A female subject age 64 · referred with a clinical suspicion of basal cell carcinoma · a dermoscopic image of a skin lesion.
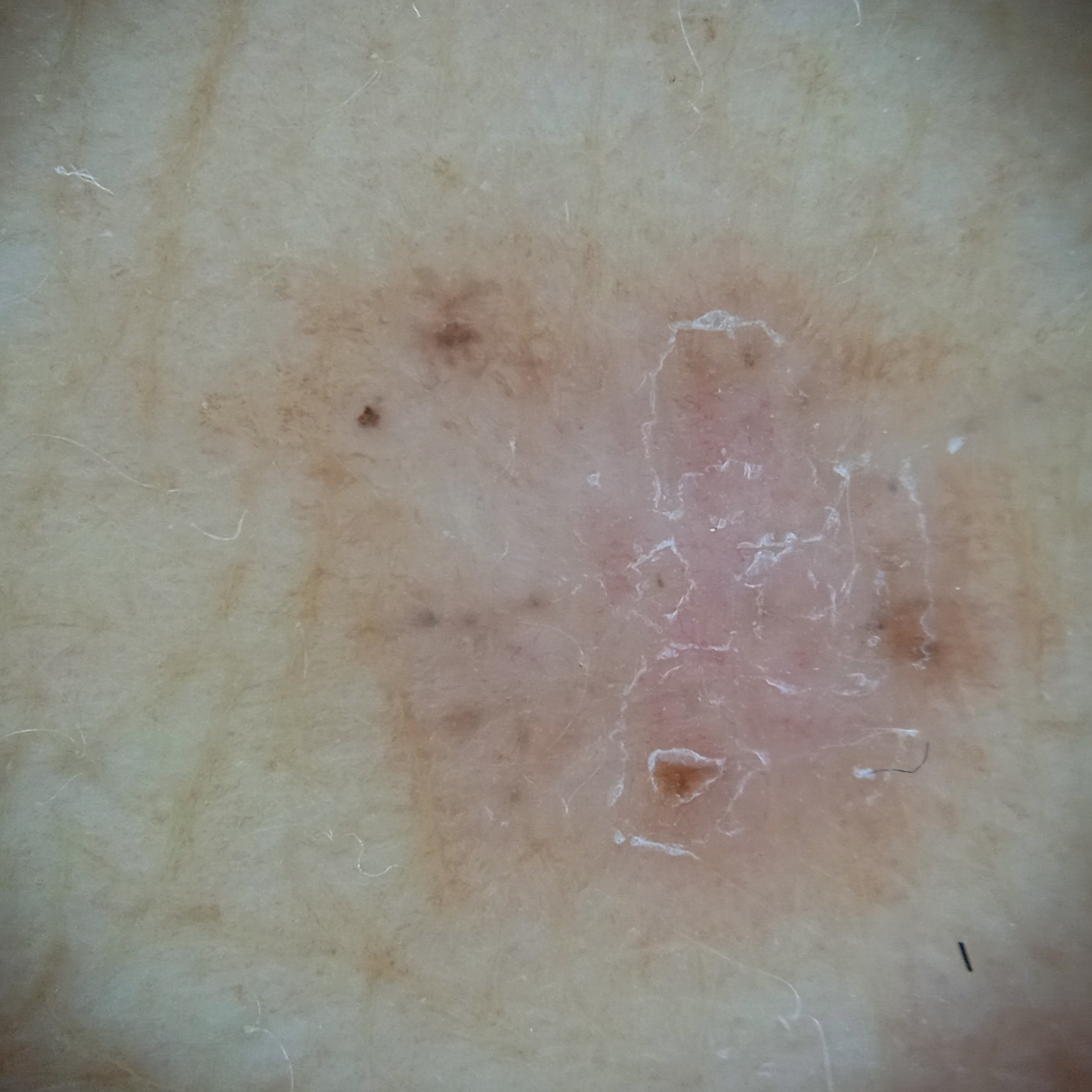anatomic site = the torso, diameter = 8.1 mm, diagnosis = basal cell carcinoma (biopsy-proven).